Imaged for a research study, with no referral diagnosis recorded; the patient says their skin tans without first burning; a male patient 72 years of age; a macroscopic clinical photograph of a skin lesion; a moderate number of moles by the patient's own estimate: 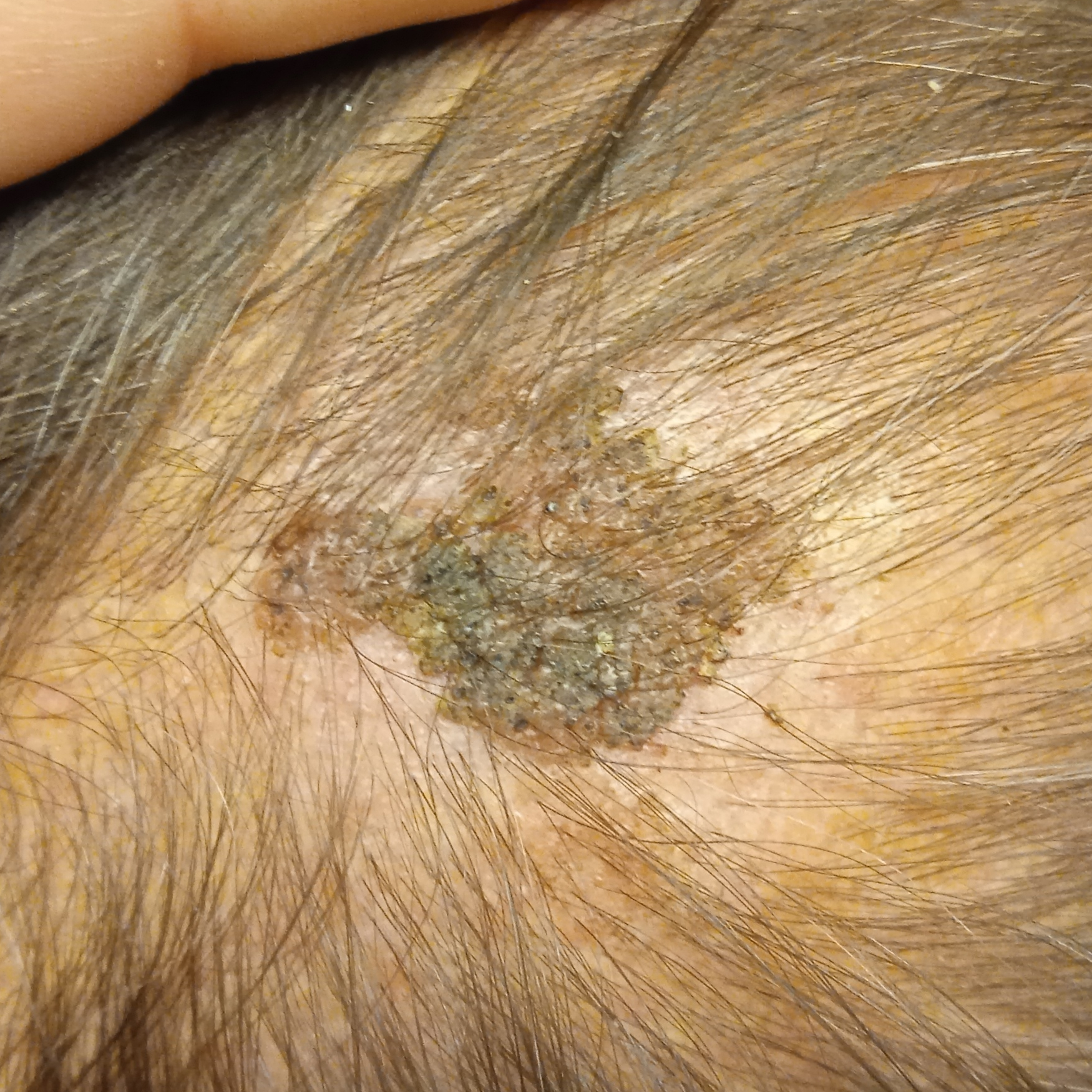body site = the head
diameter = 19.2 mm
diagnostic label = seborrheic keratosis (dermatologist consensus)